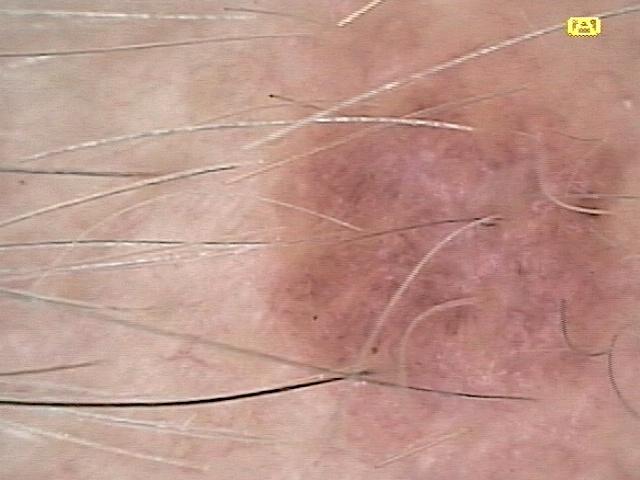<case>
<melanoma_history>
<personal_hx_melanoma>true</personal_hx_melanoma>
<family_hx_melanoma>false</family_hx_melanoma>
</melanoma_history>
<image>dermoscopic image</image>
<skin_type>II</skin_type>
<lesion_location>
<region>the head or neck</region>
</lesion_location>
<diagnosis>
<name>Nevus</name>
<malignancy>benign</malignancy>
<confirmation>histopathology</confirmation>
<lineage>melanocytic</lineage>
</diagnosis>
</case>